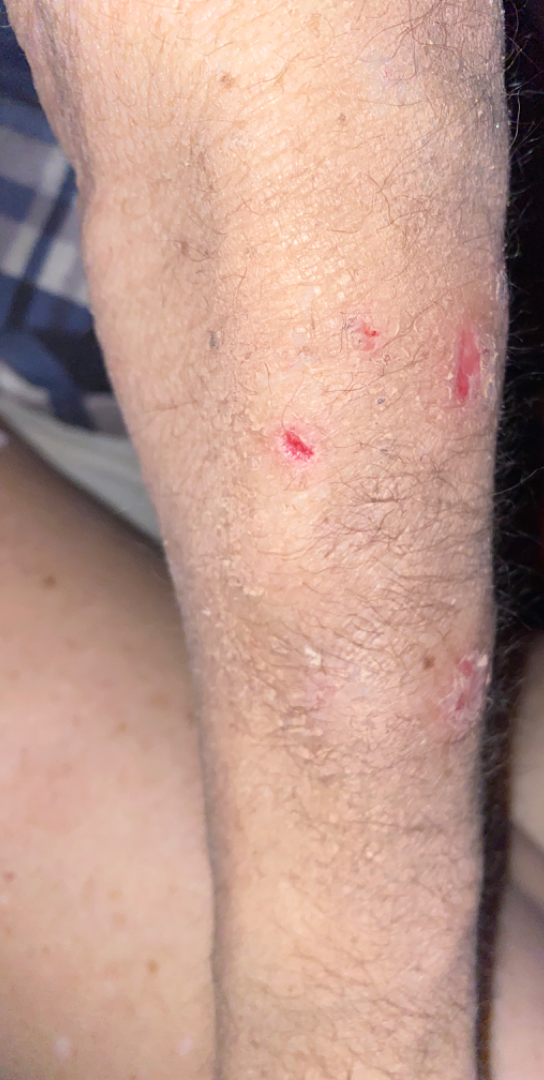Patient information: Reported duration is one to three months. The arm is involved. This is a close-up image. Review: The reviewing dermatologist's impression was: most consistent with Chronic dermatitis, NOS.